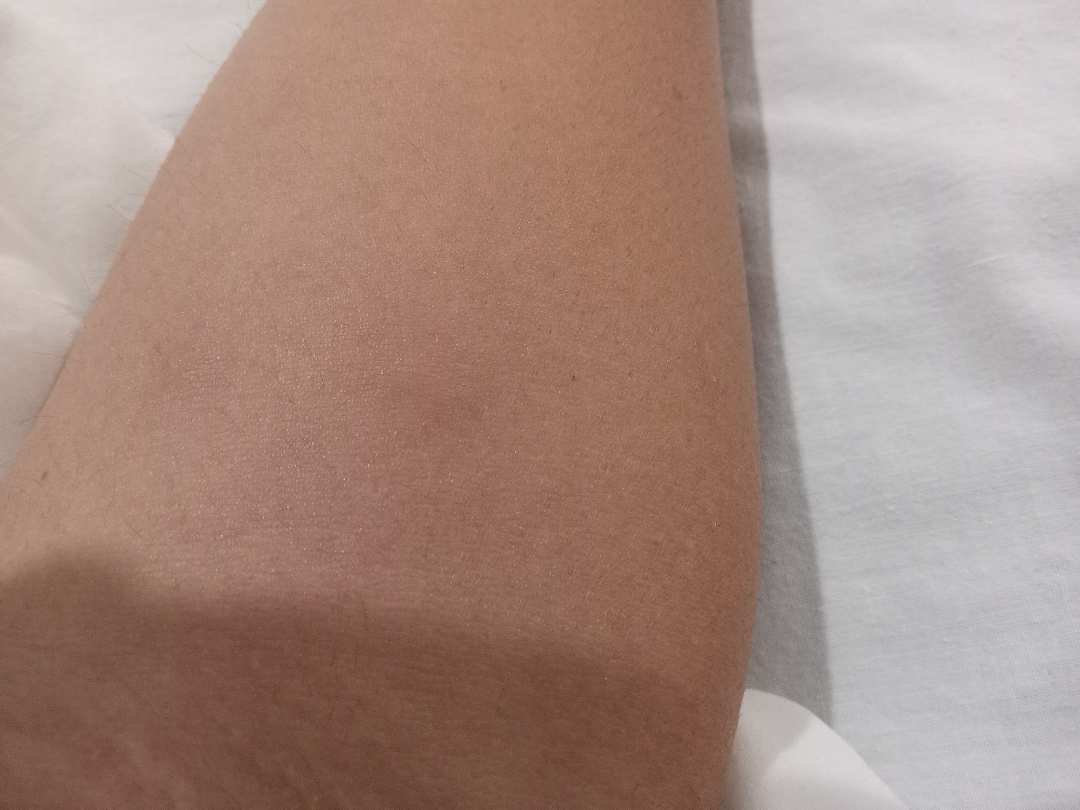{"assessment": "no findings on review", "shot_type": "close-up"}